A close-up photograph; the affected area is the leg and top or side of the foot: 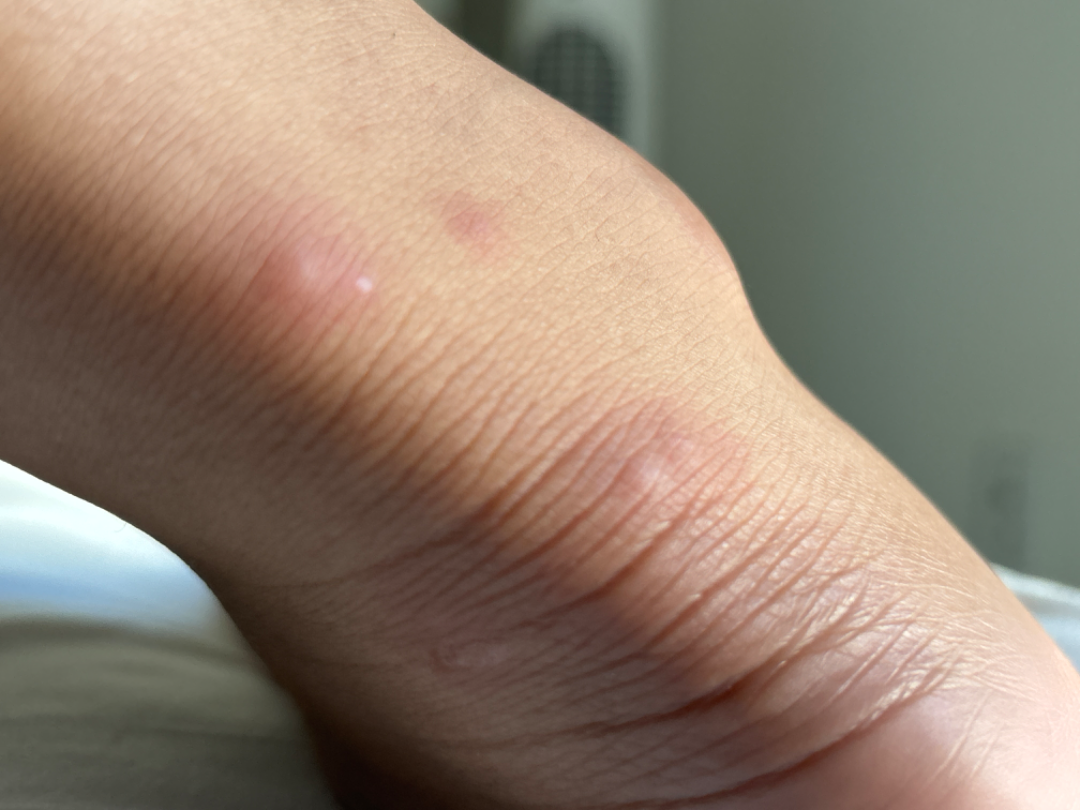<summary>
  <differential>
    <leading>Insect Bite</leading>
  </differential>
</summary>